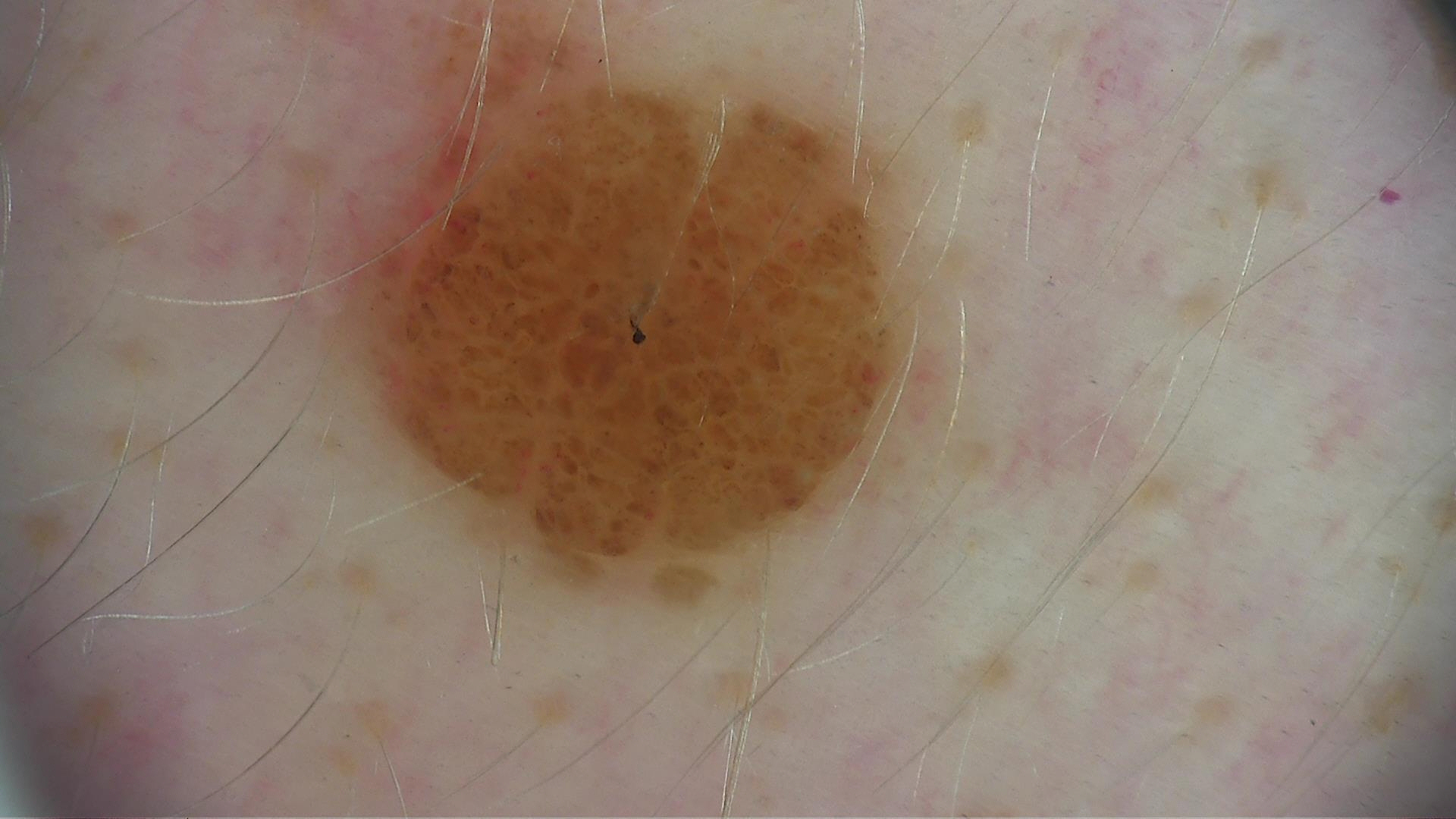Findings:
The architecture is that of a banal lesion.
Impression:
Diagnosed as a compound nevus.